A male subject in their early 80s. A clinical close-up photograph of a skin lesion: 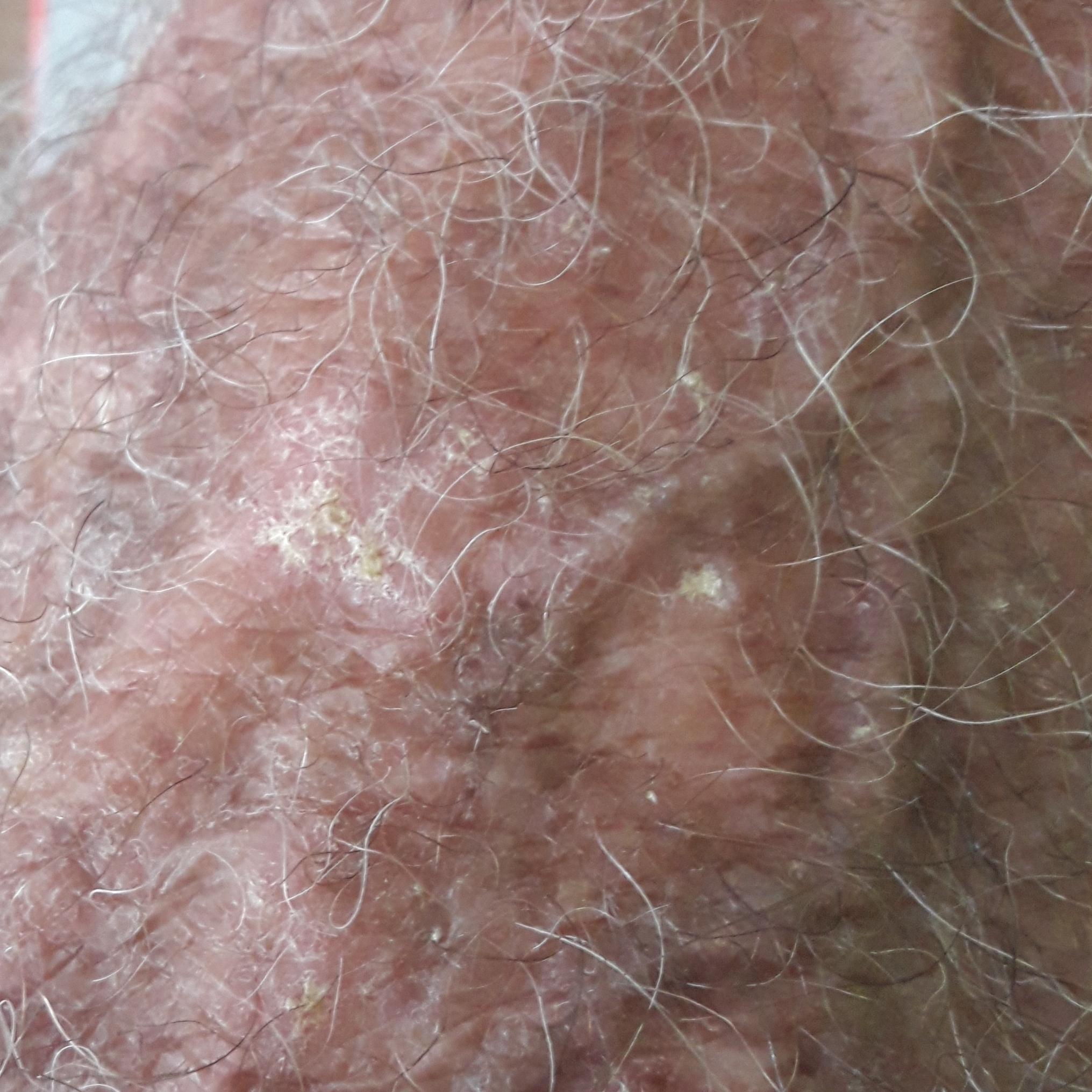body site: a hand
patient-reported symptoms: elevation / no itching, no pain
diagnostic label: actinic keratosis (clinical consensus)